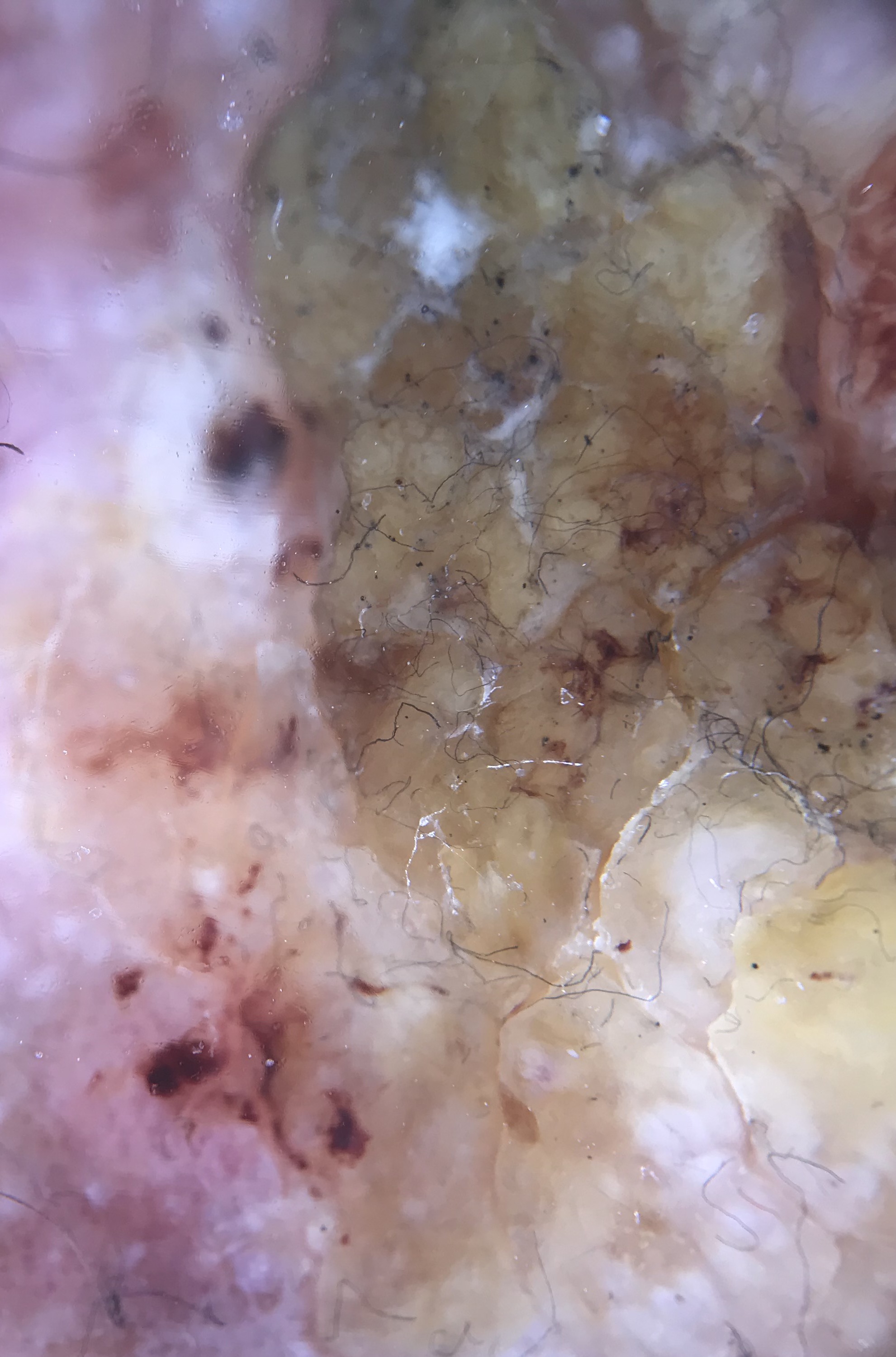modality: dermatoscopy | lesion type: keratinocytic | pathology: squamous cell carcinoma (biopsy-proven).